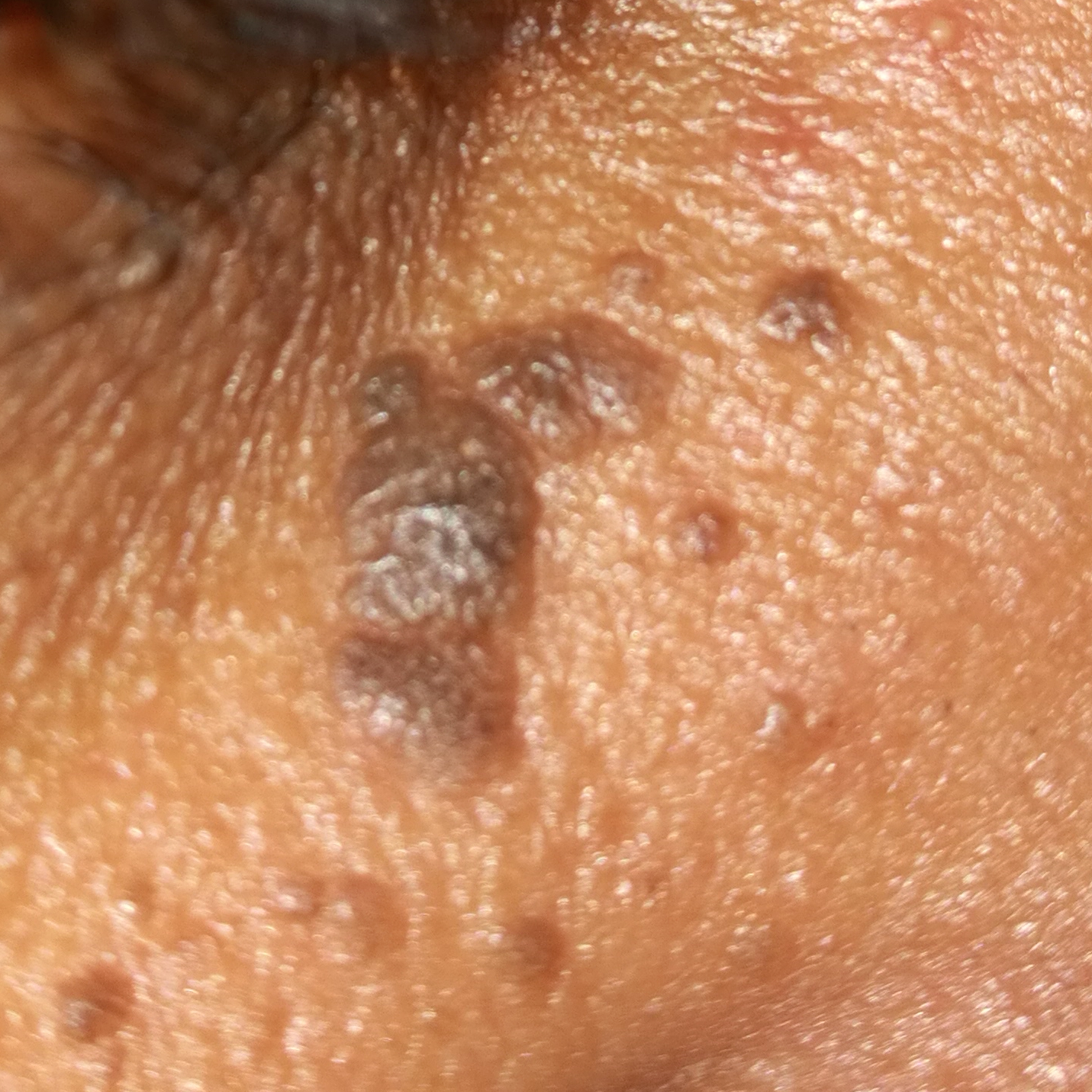lesion_location: the face
diagnosis:
  name: seborrheic keratosis
  code: SEK
  malignancy: benign
  confirmation: clinical consensus